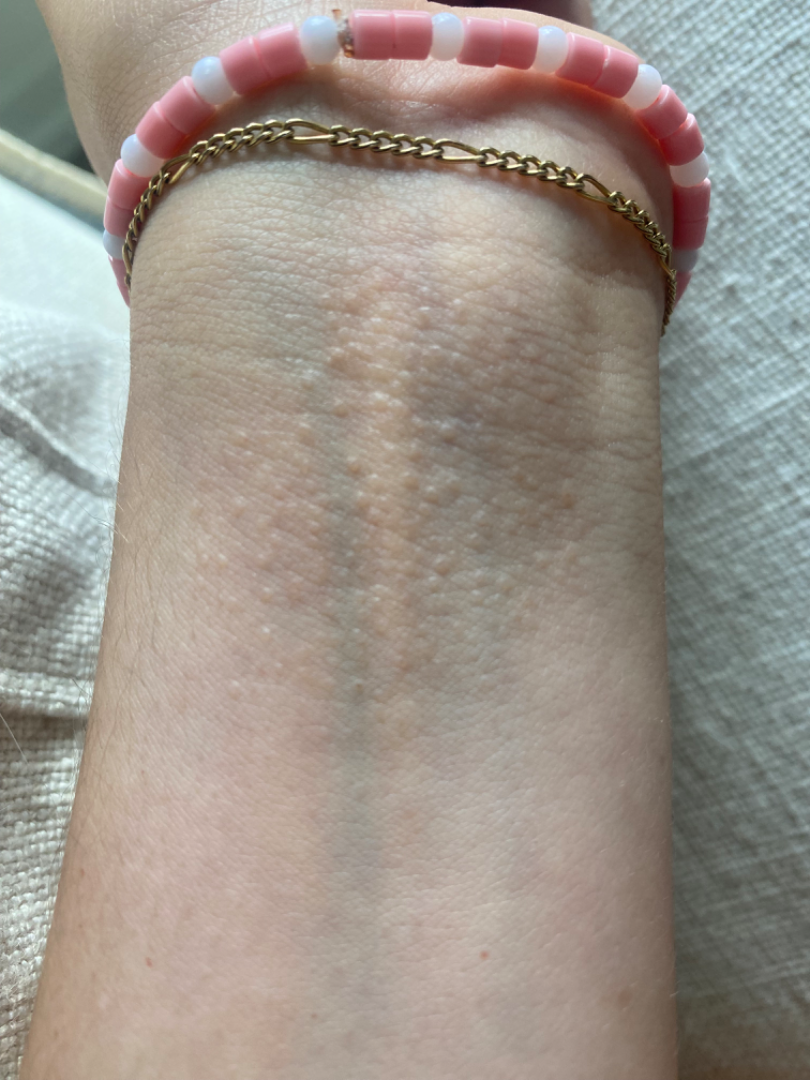texture = raised or bumpy | patient = female, age 18–29 | framing = at an angle | duration = more than one year | location = arm and top or side of the foot | systemic symptoms = none reported | clinical impression = three dermatologists independently reviewed the case: the leading consideration is Lichen nitidus; possibly Lichen Simplex Chronicus; an alternative is Eczema.